A patient age 39: 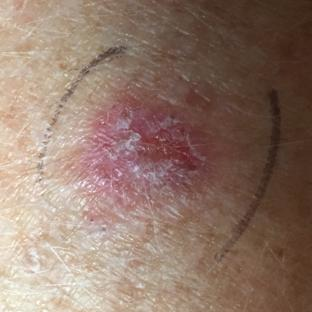Clinically diagnosed as an actinic keratosis.